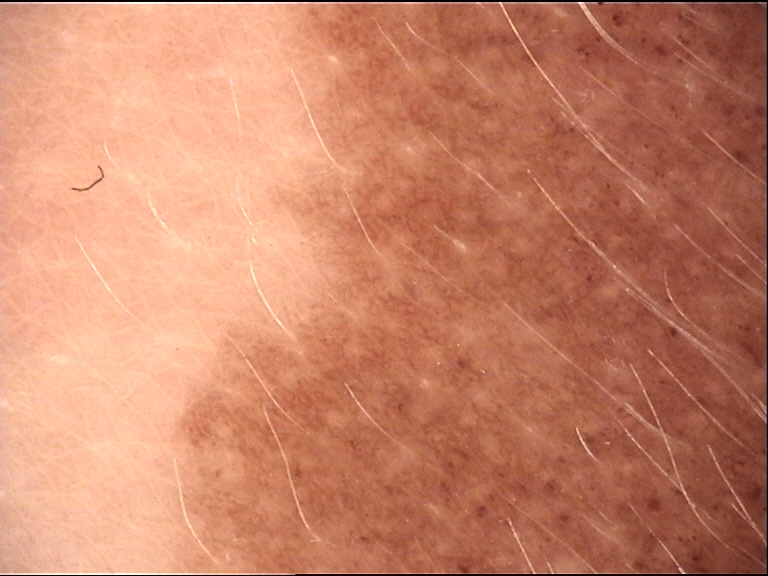Case:
– image: dermoscopy
– lesion type: banal
– diagnosis: congenital junctional nevus (expert consensus)